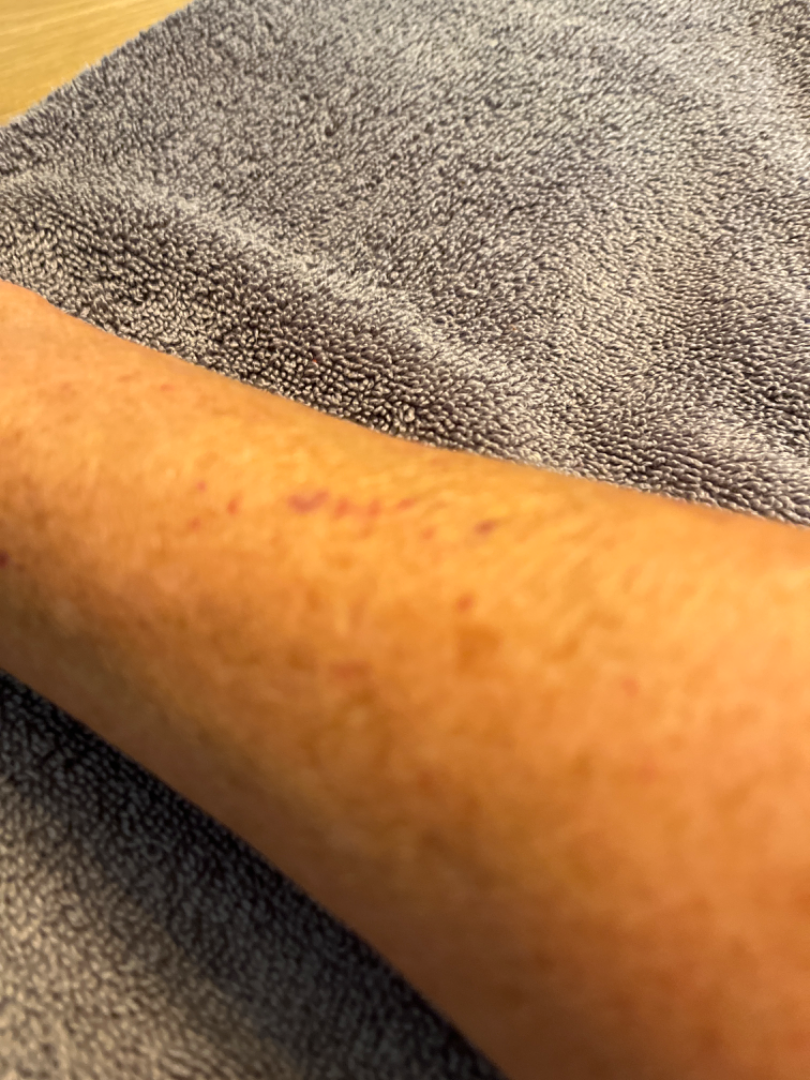The skin condition could not be confidently assessed from this image.
The arm is involved.
The patient is a female aged 60–69.
This is a close-up image.